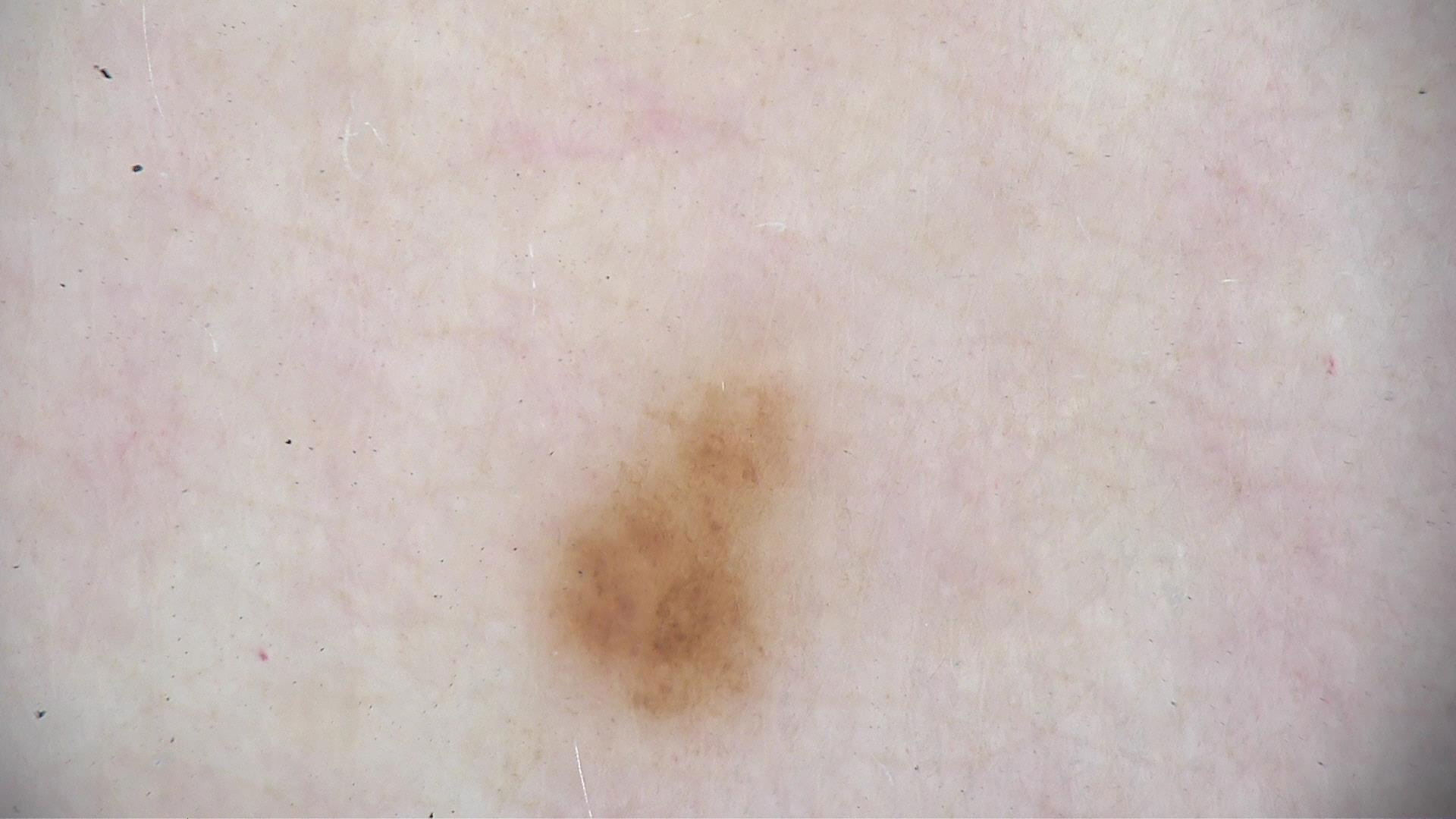| field | value |
|---|---|
| class | dysplastic junctional nevus (expert consensus) |